Texture is reported as raised or bumpy · the patient is 50–59, female · no associated systemic symptoms reported · the photograph is a close-up of the affected area · present for less than one week · the arm and palm are involved.
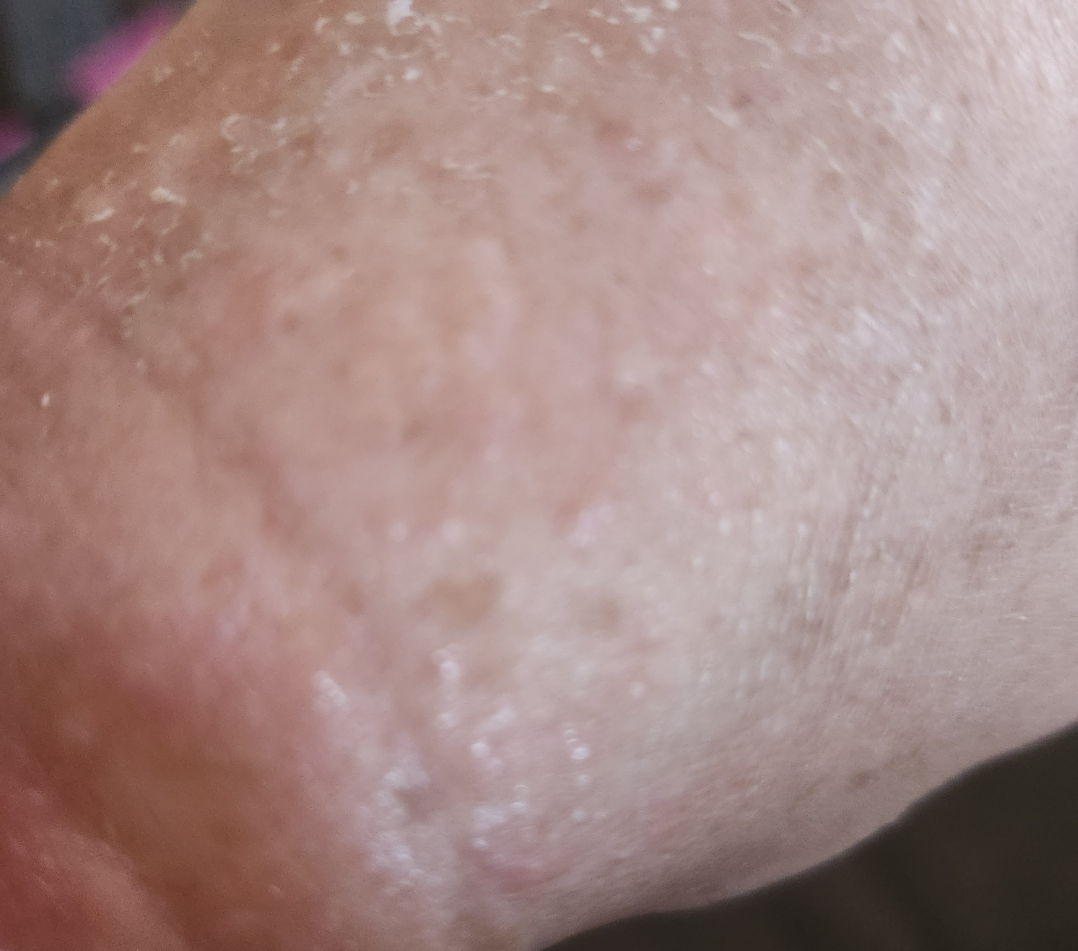assessment=ungradable on photographic review.